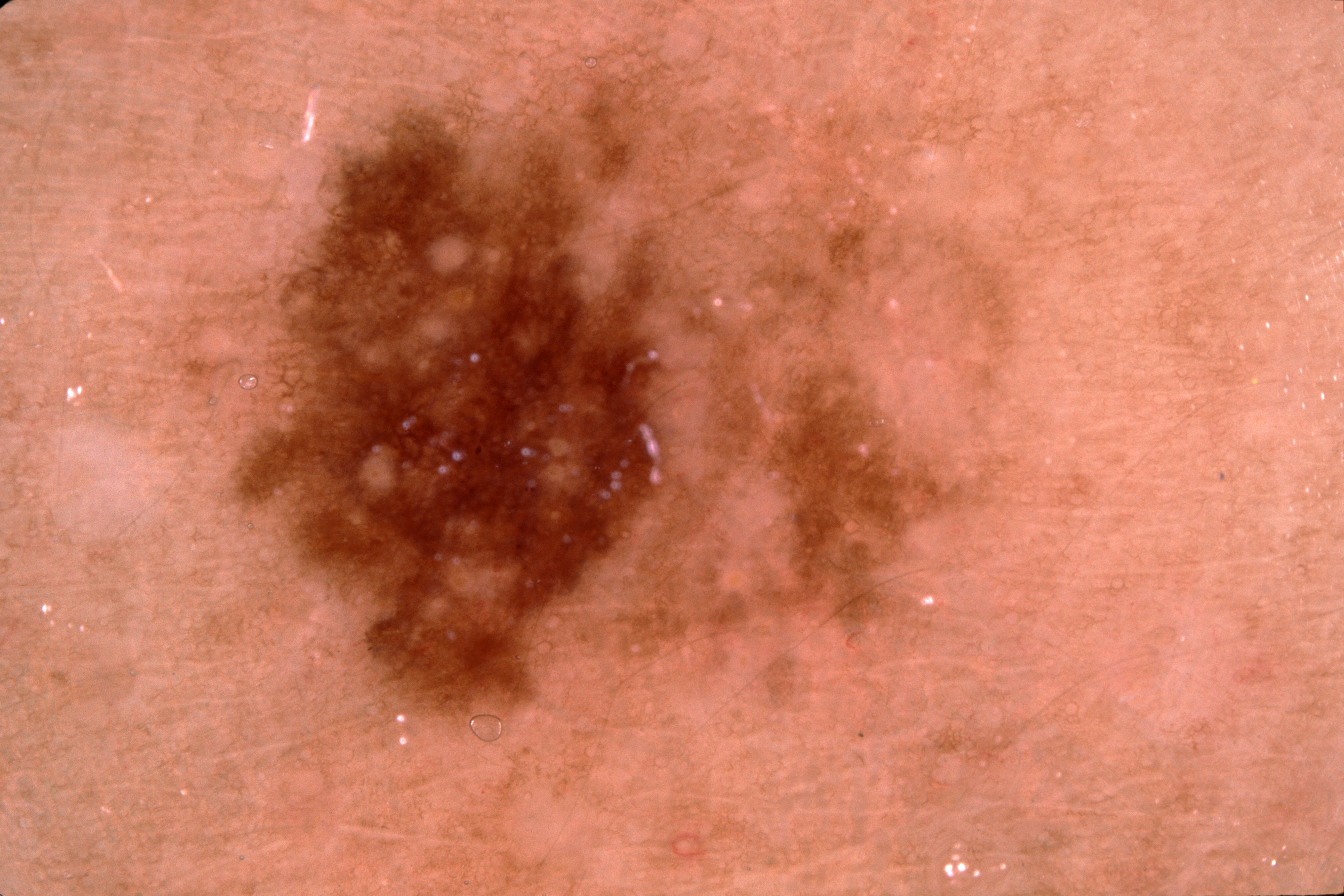Q: Who is the patient?
A: female, in their mid-40s
Q: What kind of image is this?
A: dermatoscopic image of a skin lesion
Q: What does dermoscopy show?
A: pigment network
Q: Where is the lesion in the image?
A: box(766, 373, 907, 621)
Q: Lesion extent?
A: ~1% of the field
Q: What did the assessment conclude?
A: a melanoma